A skin lesion imaged with a dermatoscope: 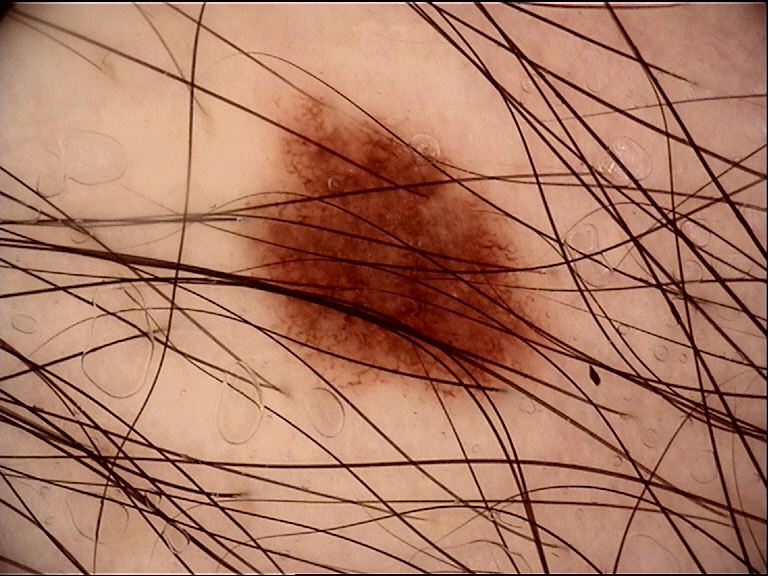| feature | finding |
|---|---|
| label | dysplastic junctional nevus (expert consensus) |